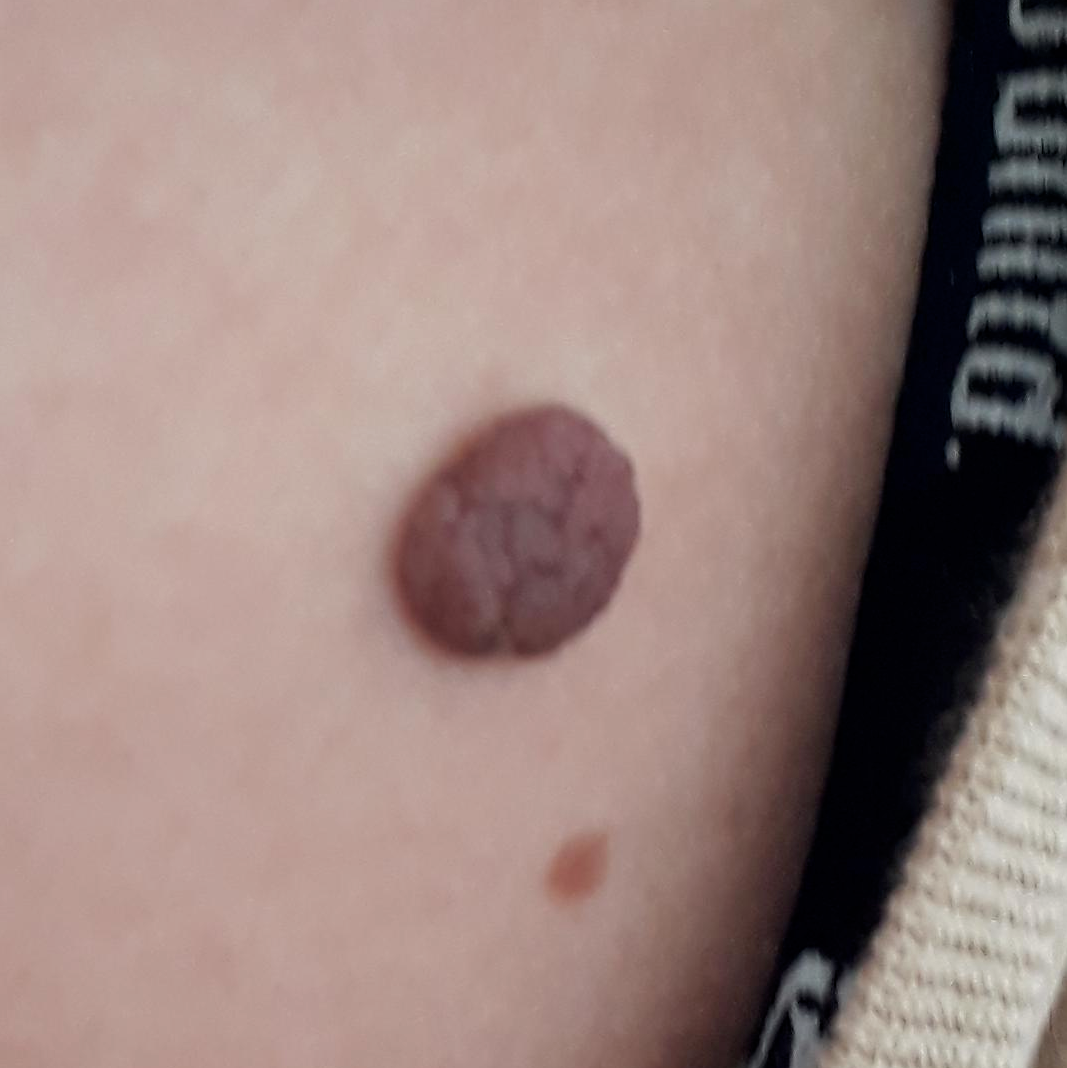location = the back
patient-reported symptoms = growth, elevation / no bleeding
diagnosis = nevus (clinical consensus)